A skin lesion imaged with a dermatoscope: 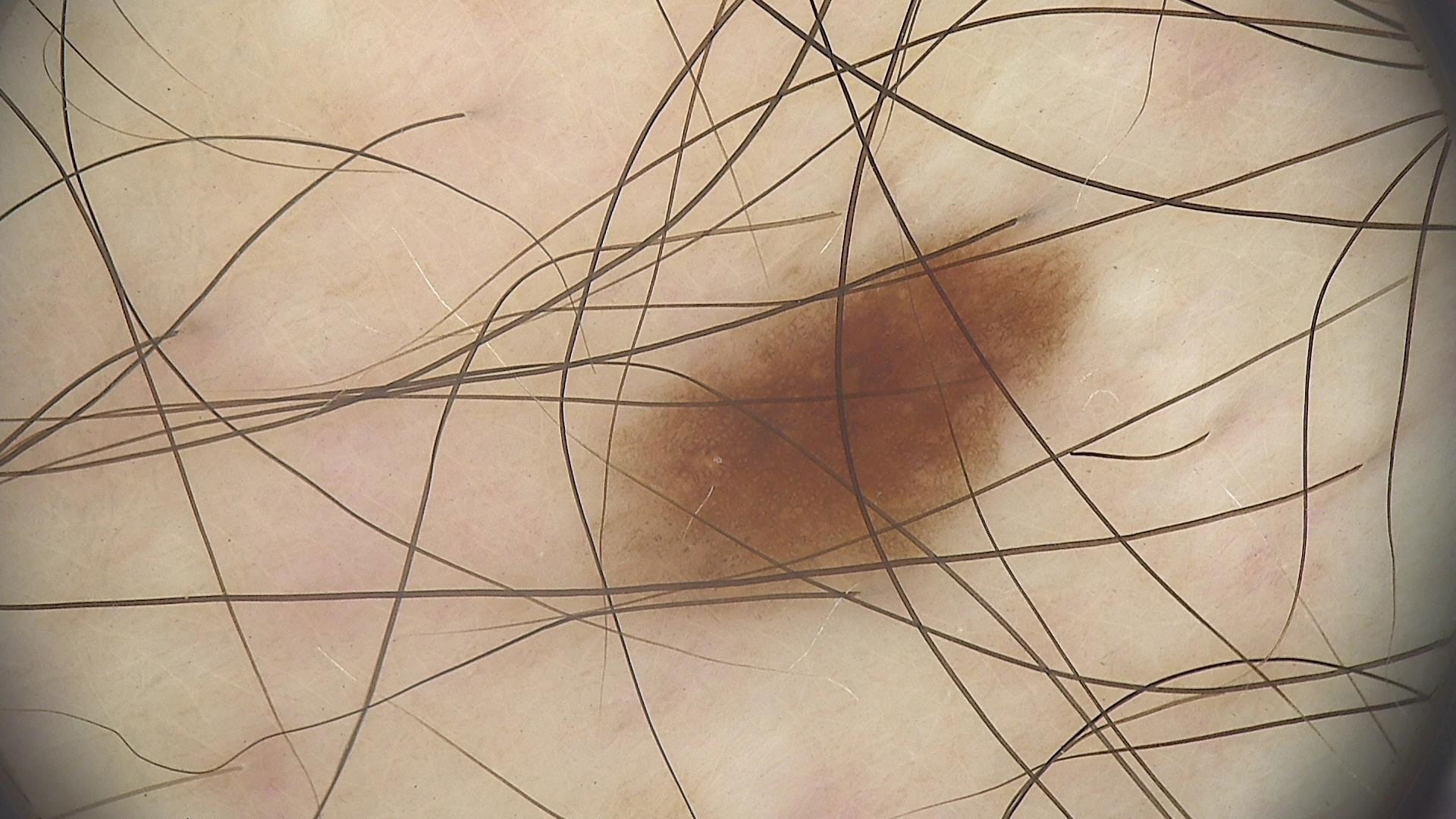label = dysplastic junctional nevus (expert consensus).